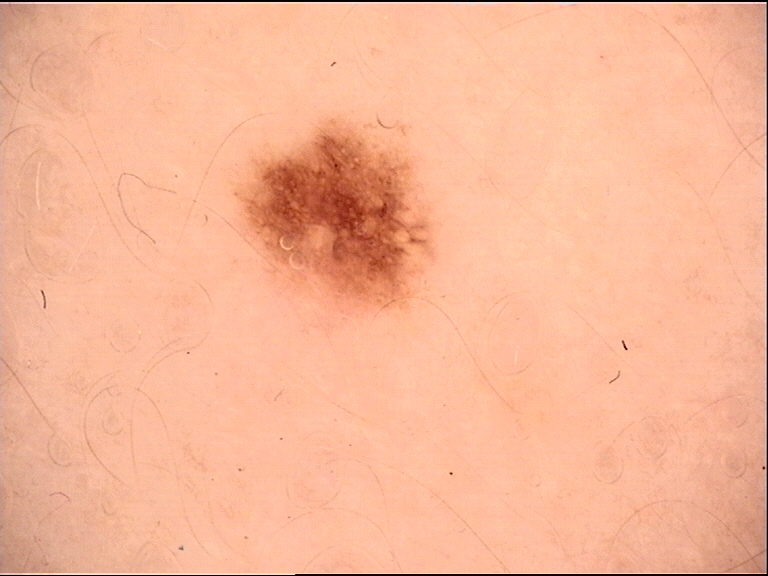Summary: A dermoscopic photograph of a skin lesion. Conclusion: Consistent with a benign lesion — a dysplastic junctional nevus.